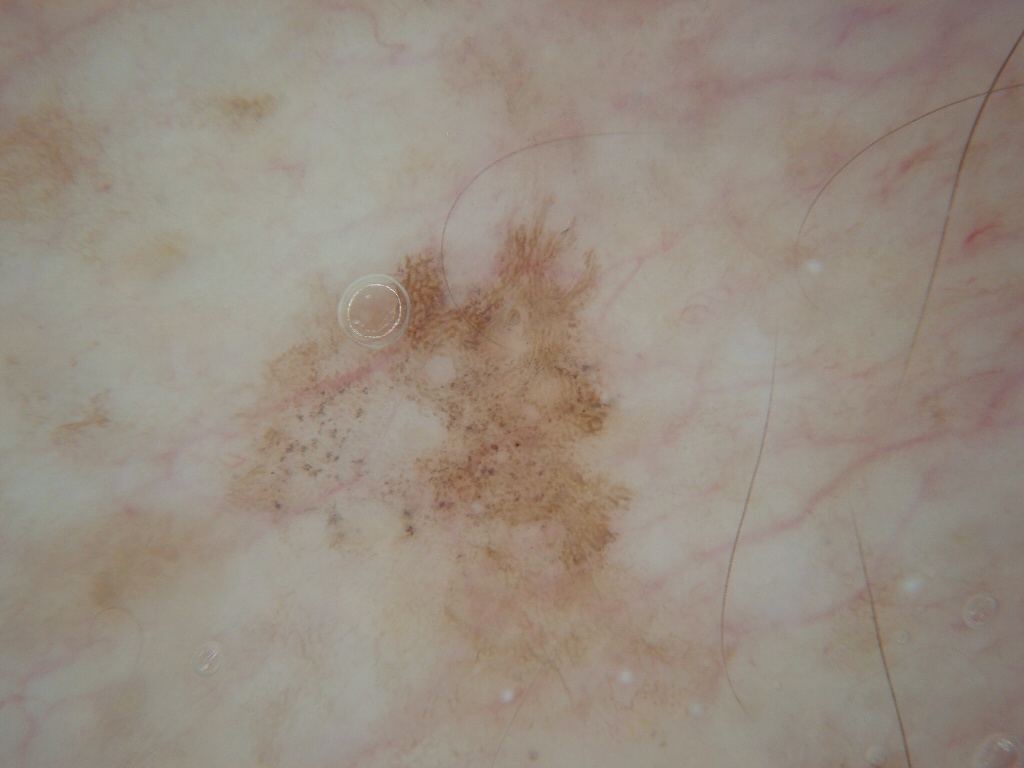A dermoscopic image of a skin lesion. The lesion occupies the region bbox(213, 179, 653, 620). Dermoscopic review identifies no globules or streaks. The diagnostic assessment was a benign lesion.